Dermoscopy of a skin lesion:
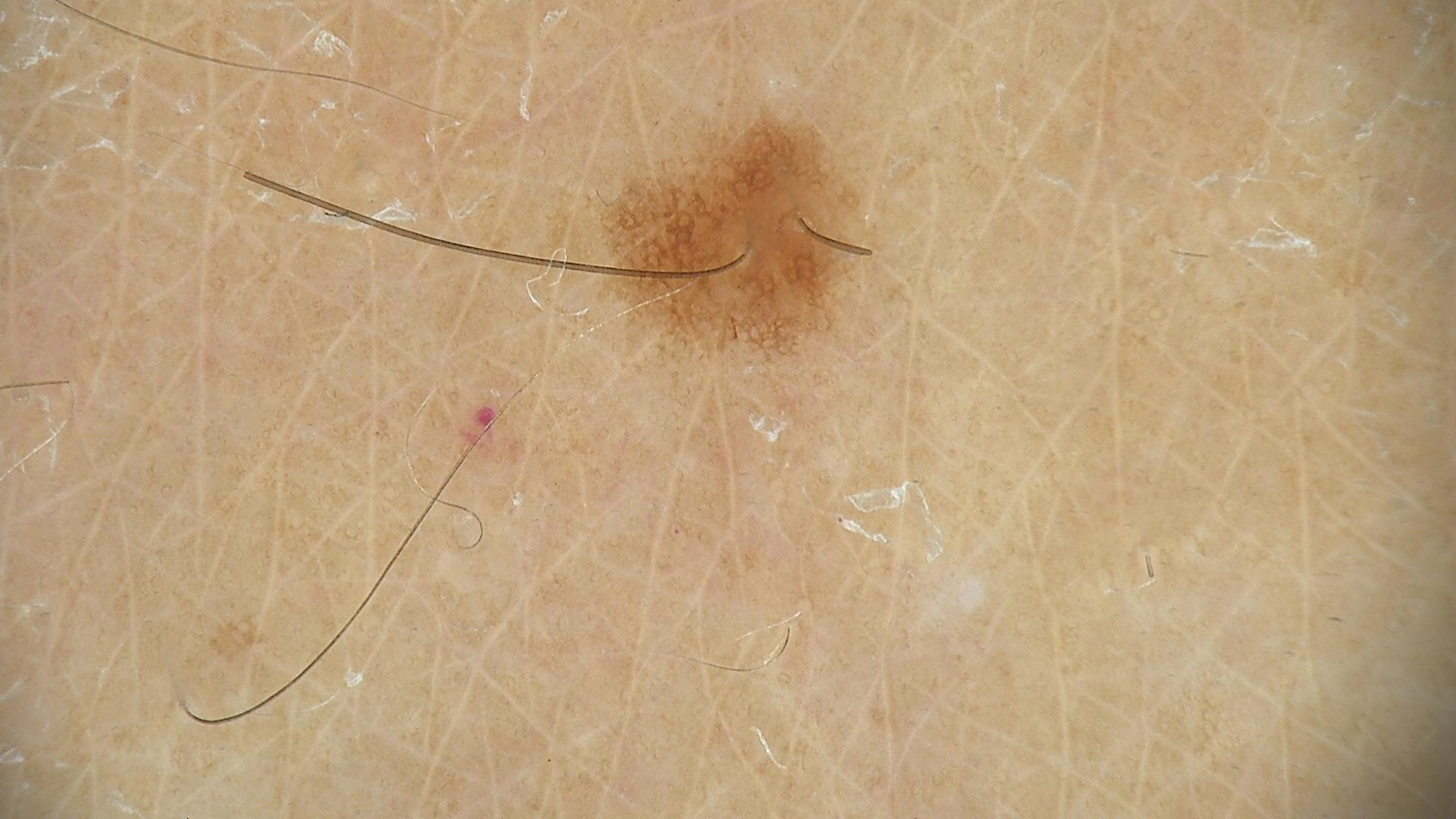diagnostic label: dysplastic junctional nevus (expert consensus)